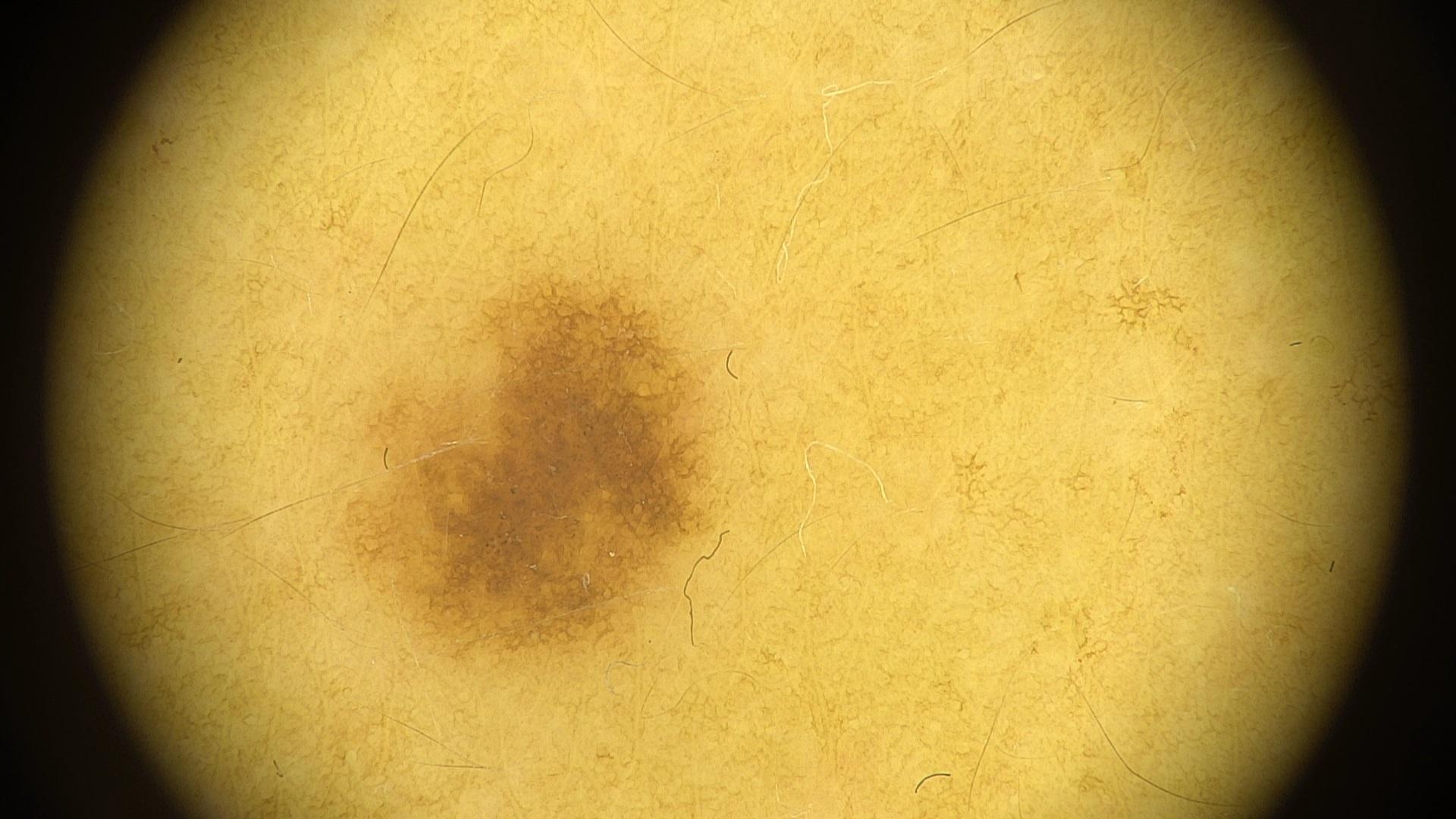subject = female, aged 33-37 | imaging = contact-polarized dermoscopy | anatomic site = the trunk | diagnostic label = Nevus (clinical impression).